A skin lesion imaged with a dermatoscope.
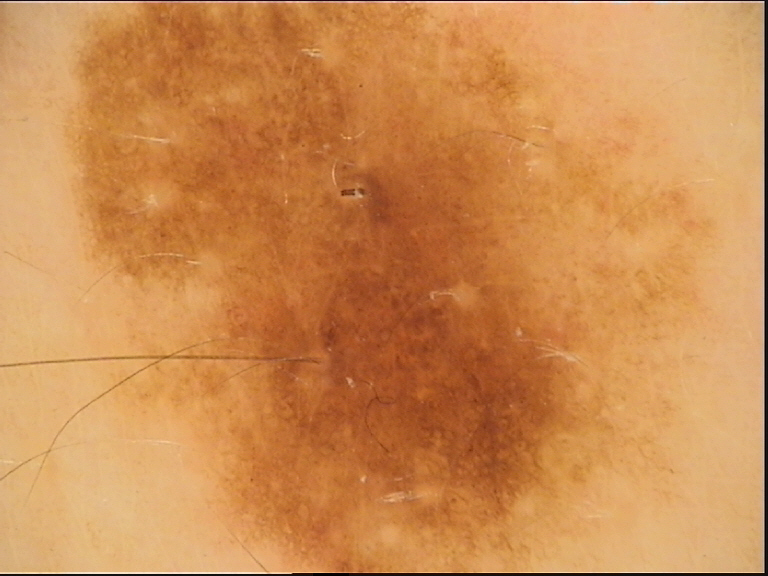label: dysplastic junctional nevus (expert consensus).